A subject in their early 80s. A clinical close-up photograph of a skin lesion:
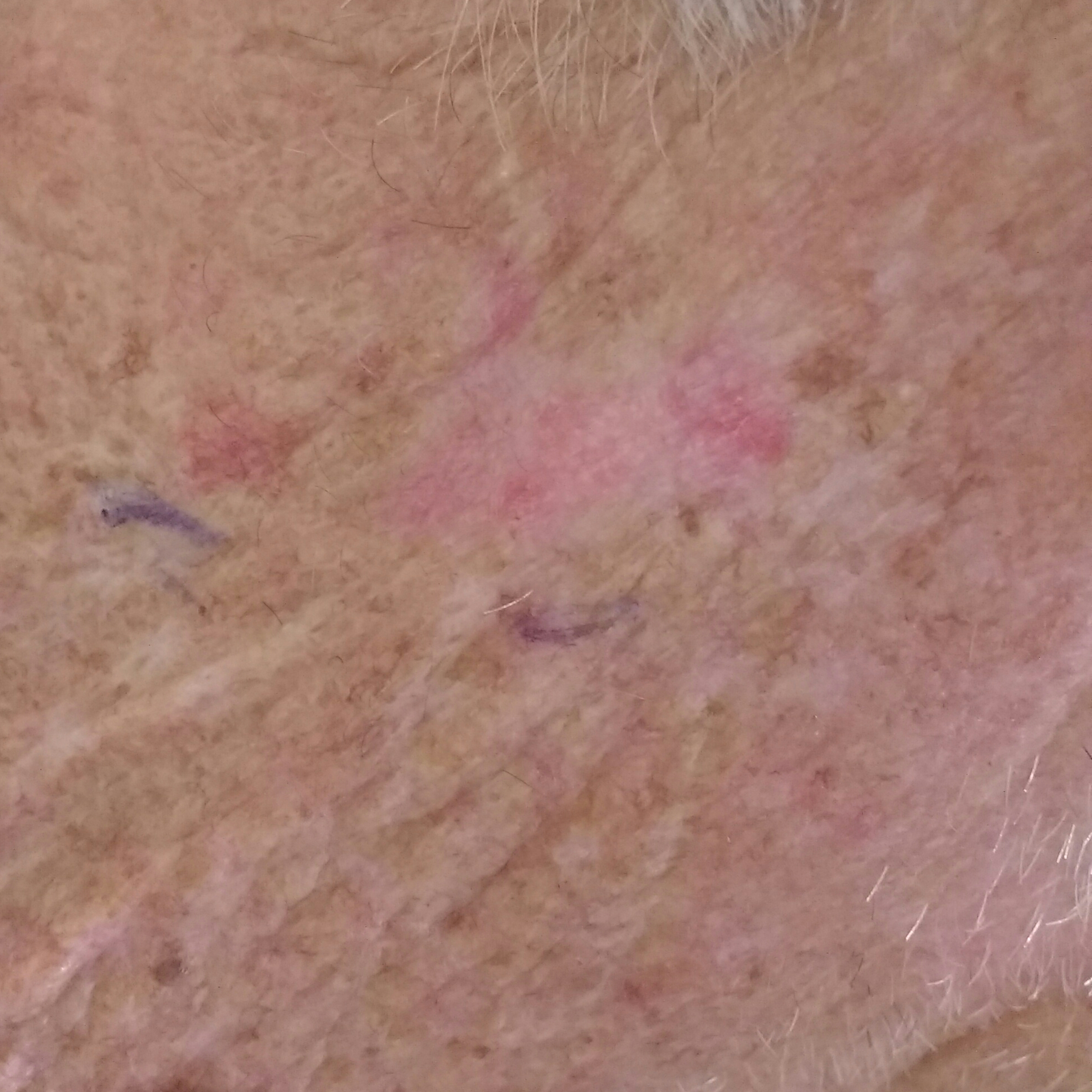Located on the neck. By the patient's account, the lesion itches. Clinically diagnosed as an actinic keratosis.